Located on the leg, the patient considered this a rash, the contributor notes the condition has been present for about one day, Fitzpatrick phototype II; non-clinician graders estimated MST 1 or 2, the photograph was taken at an angle, the patient reported no systemic symptoms, the lesion is described as raised or bumpy, the contributor notes itching: 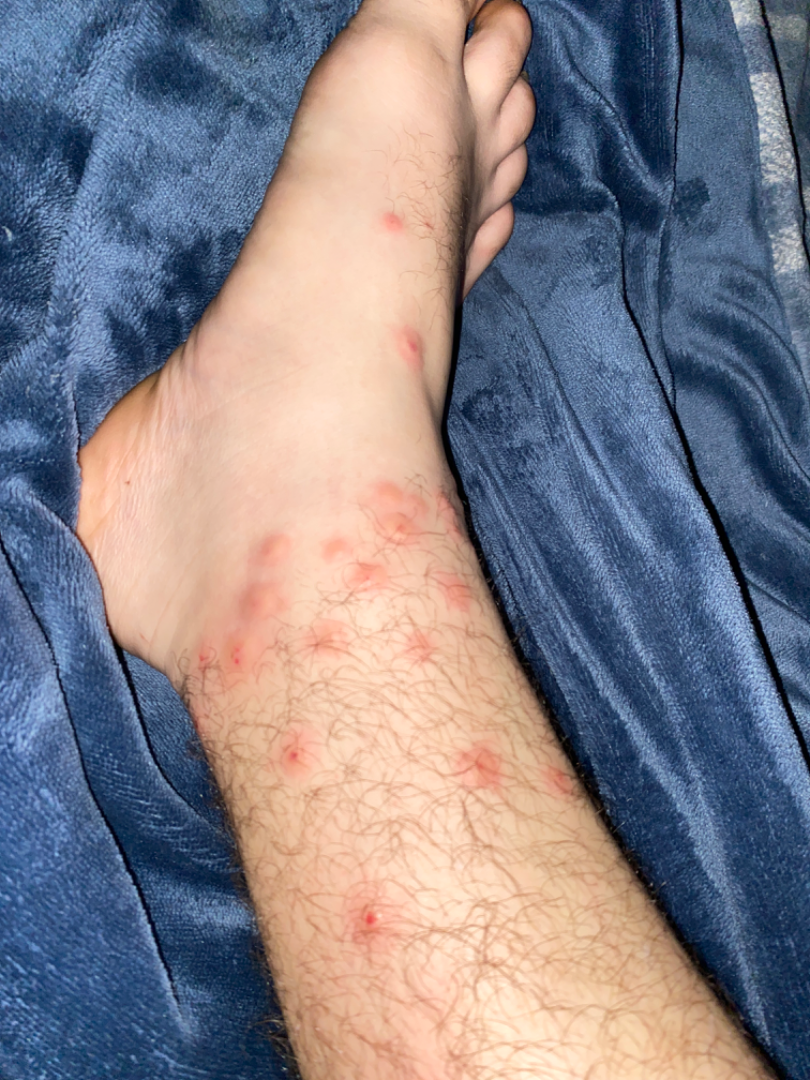Notes:
– assessment: indeterminate from the photograph